The patient is Fitzpatrick phototype II · a smartphone photograph of a skin lesion · the chart notes pesticide exposure · a male subject aged 87: 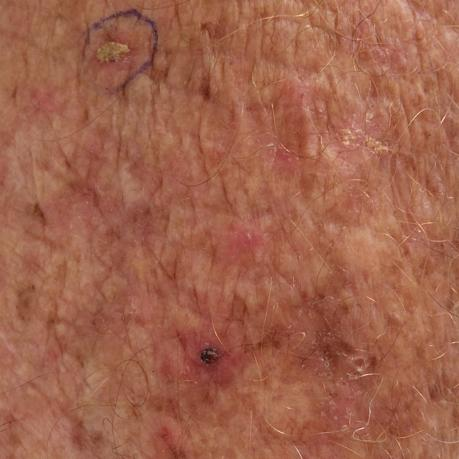body site: a forearm; lesion size: 10x10 mm; patient-reported symptoms: bleeding, itching, elevation; impression: actinic keratosis (clinical consensus).